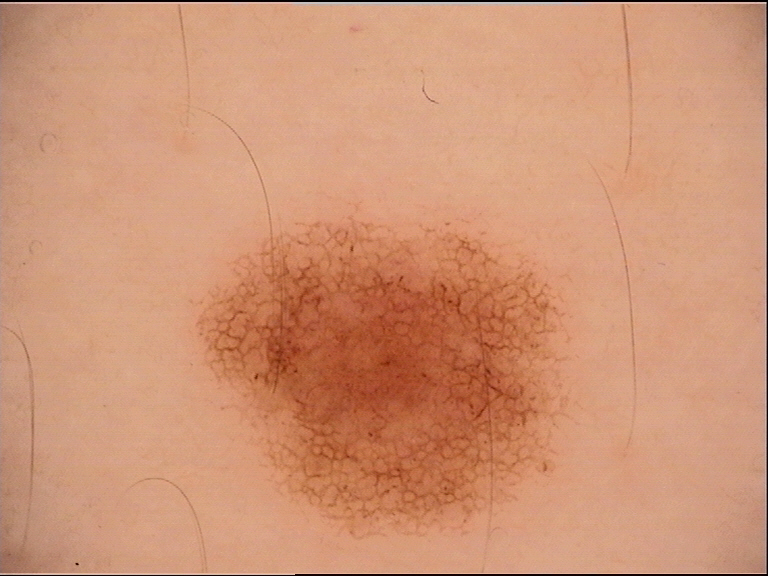Consistent with a dysplastic junctional nevus.